The condition has been present for one to three months. The patient notes itching, bothersome appearance, pain, burning and enlargement. The patient described the issue as a rash. This is a close-up image. The lesion involves the back of the torso and arm. Texture is reported as raised or bumpy and rough or flaky. The patient is a female aged 40–49.
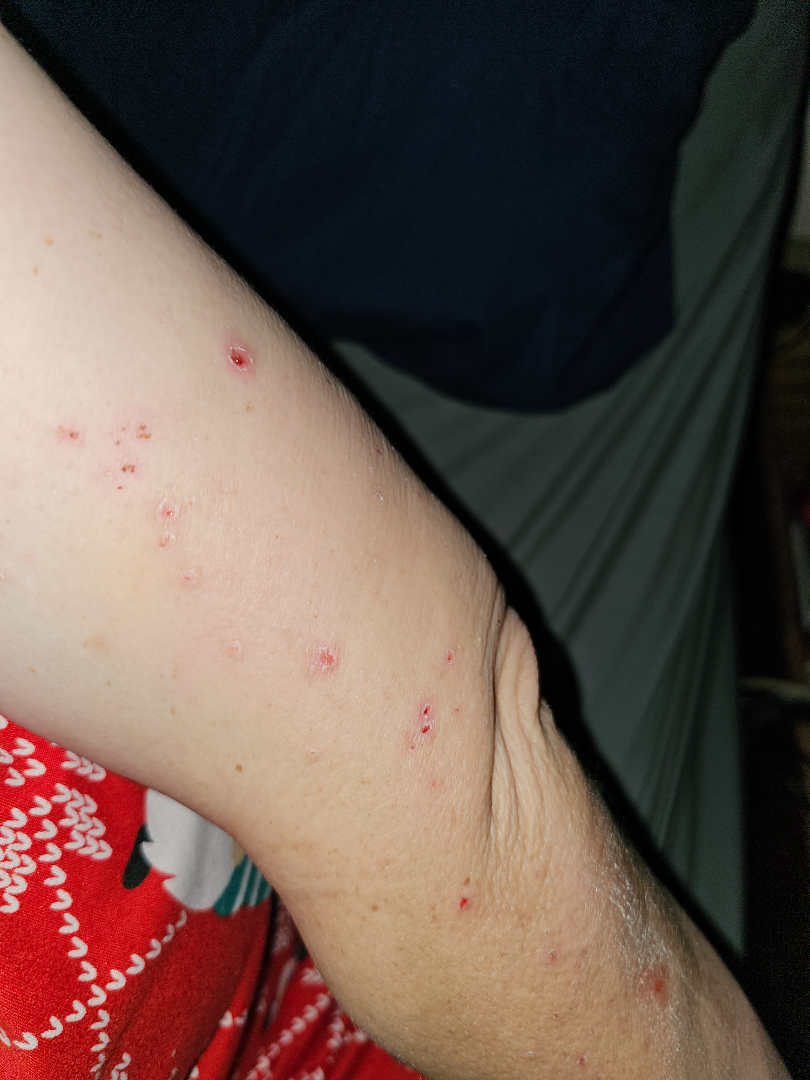| feature | finding |
|---|---|
| differential diagnosis | most consistent with Eczema |